Dermoscopy of a skin lesion.
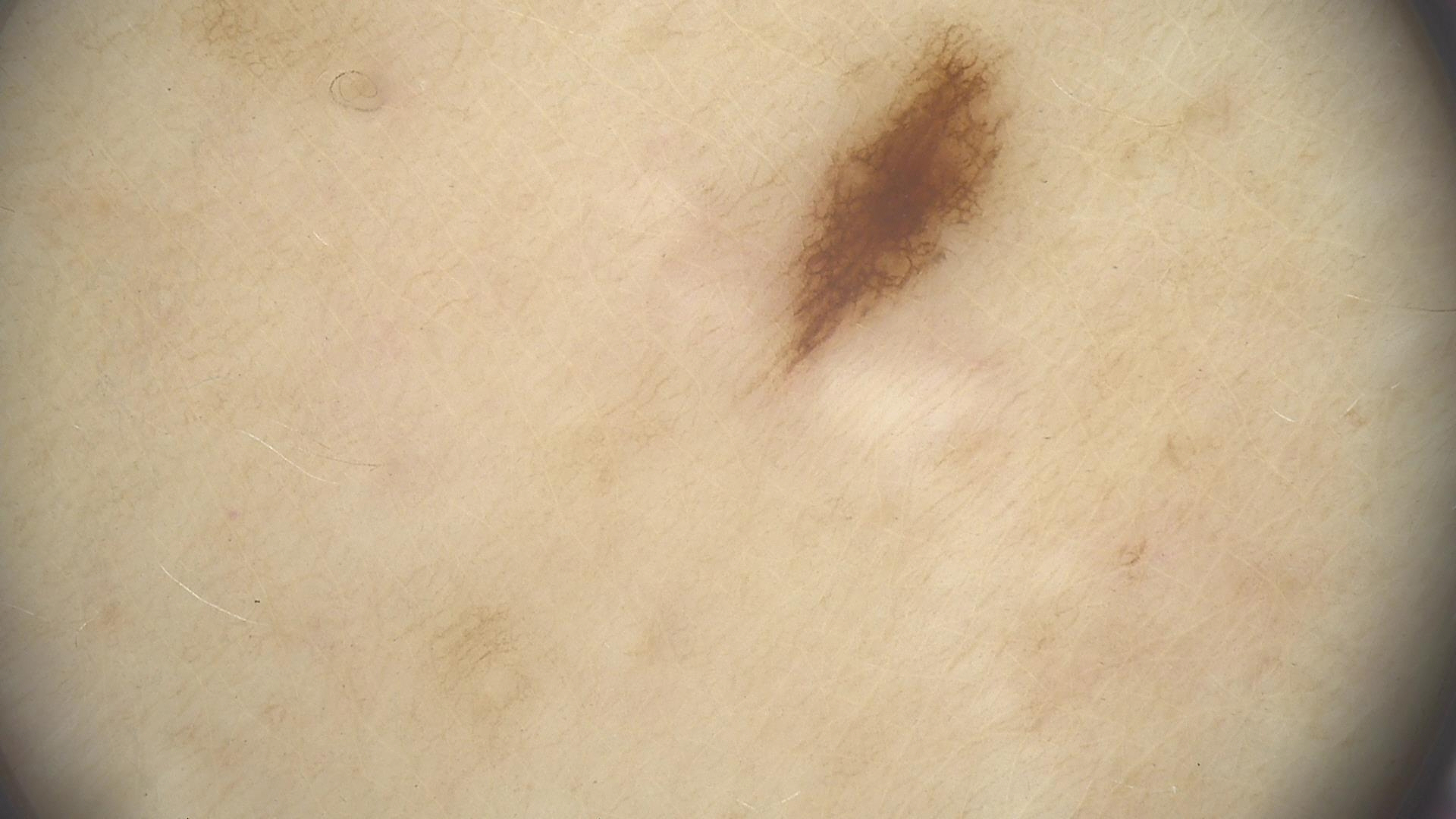Consistent with a dysplastic junctional nevus.